A dermoscopy image of a single skin lesion; a male patient, aged approximately 40 — 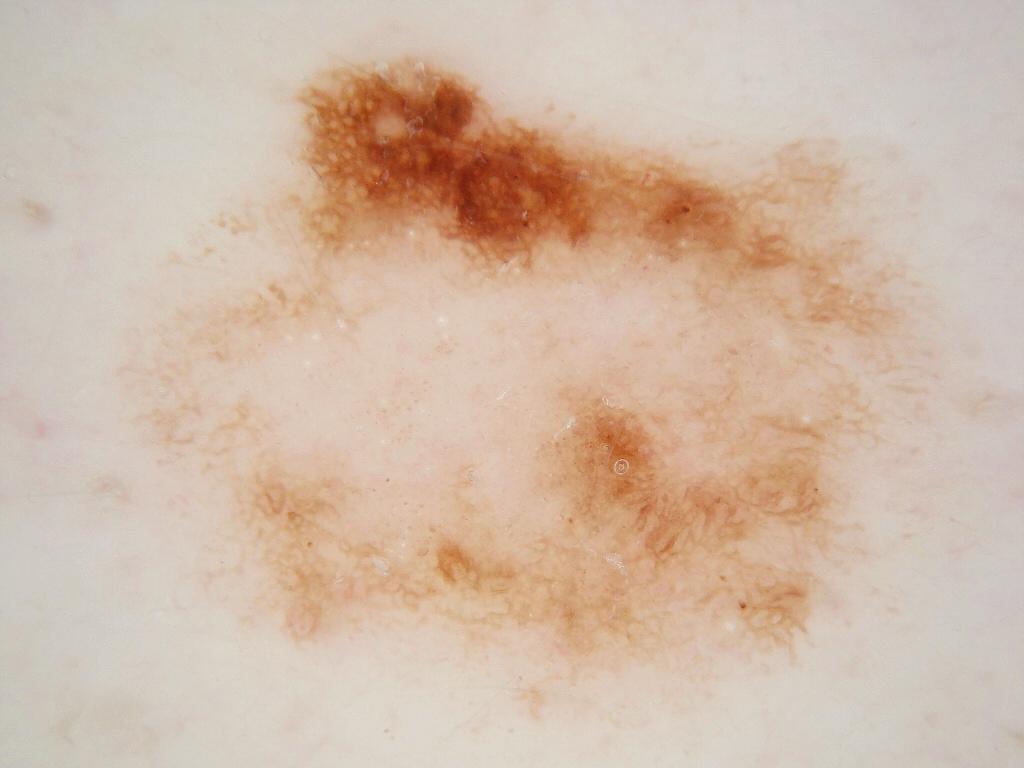The lesion is located at x1=82 y1=43 x2=999 y2=733. A large lesion occupying much of the field. The dermoscopic pattern shows pigment network and milia-like cysts. Consistent with a melanocytic nevus, a benign skin lesion.